A dermatoscopic image of a skin lesion:
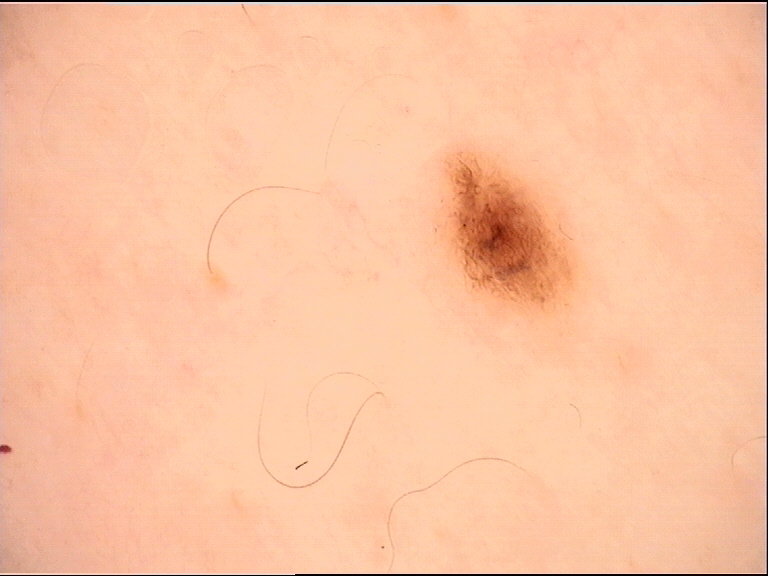Labeled as a benign lesion — a dysplastic junctional nevus.